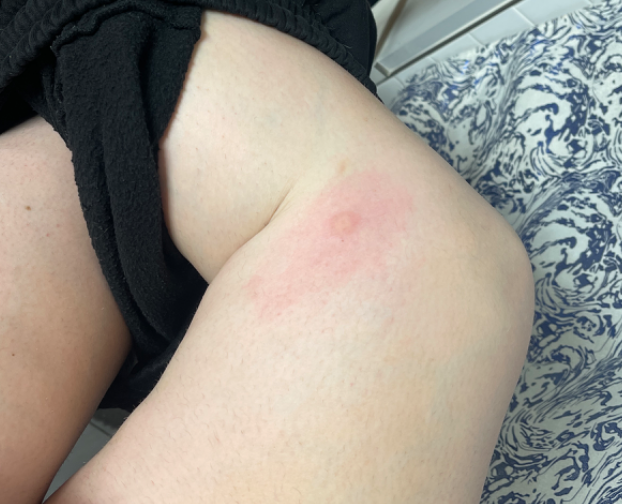<dermatology_case>
<assessment>not assessable</assessment>
<symptoms>enlargement, itching</symptoms>
<duration>about one day</duration>
<shot_type>at a distance</shot_type>
<body_site>leg</body_site>
<texture>raised or bumpy</texture>
<systemic_symptoms>none reported</systemic_symptoms>
<patient_category>a rash</patient_category>
</dermatology_case>